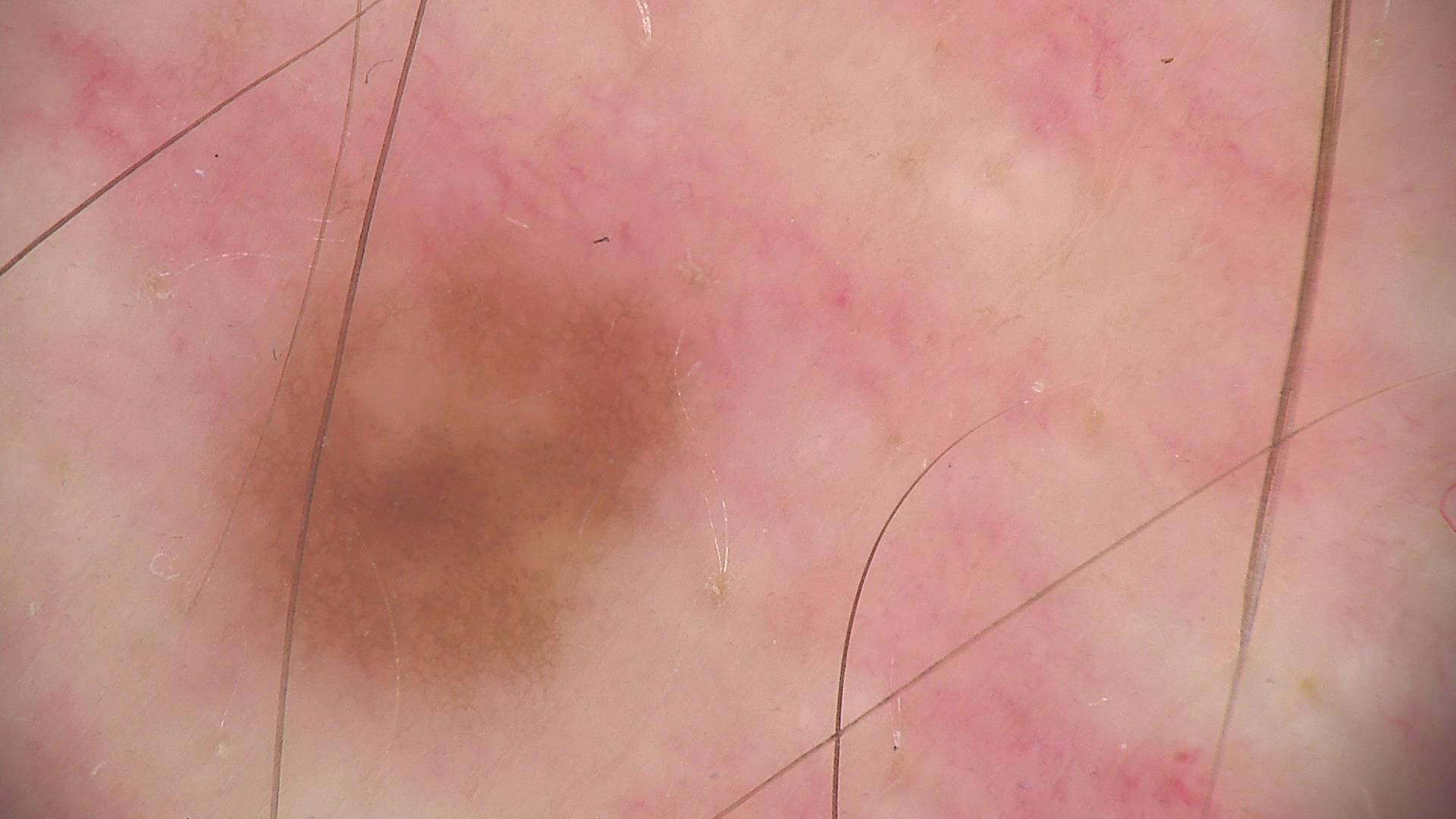image: dermatoscopy | assessment: dysplastic junctional nevus (expert consensus).